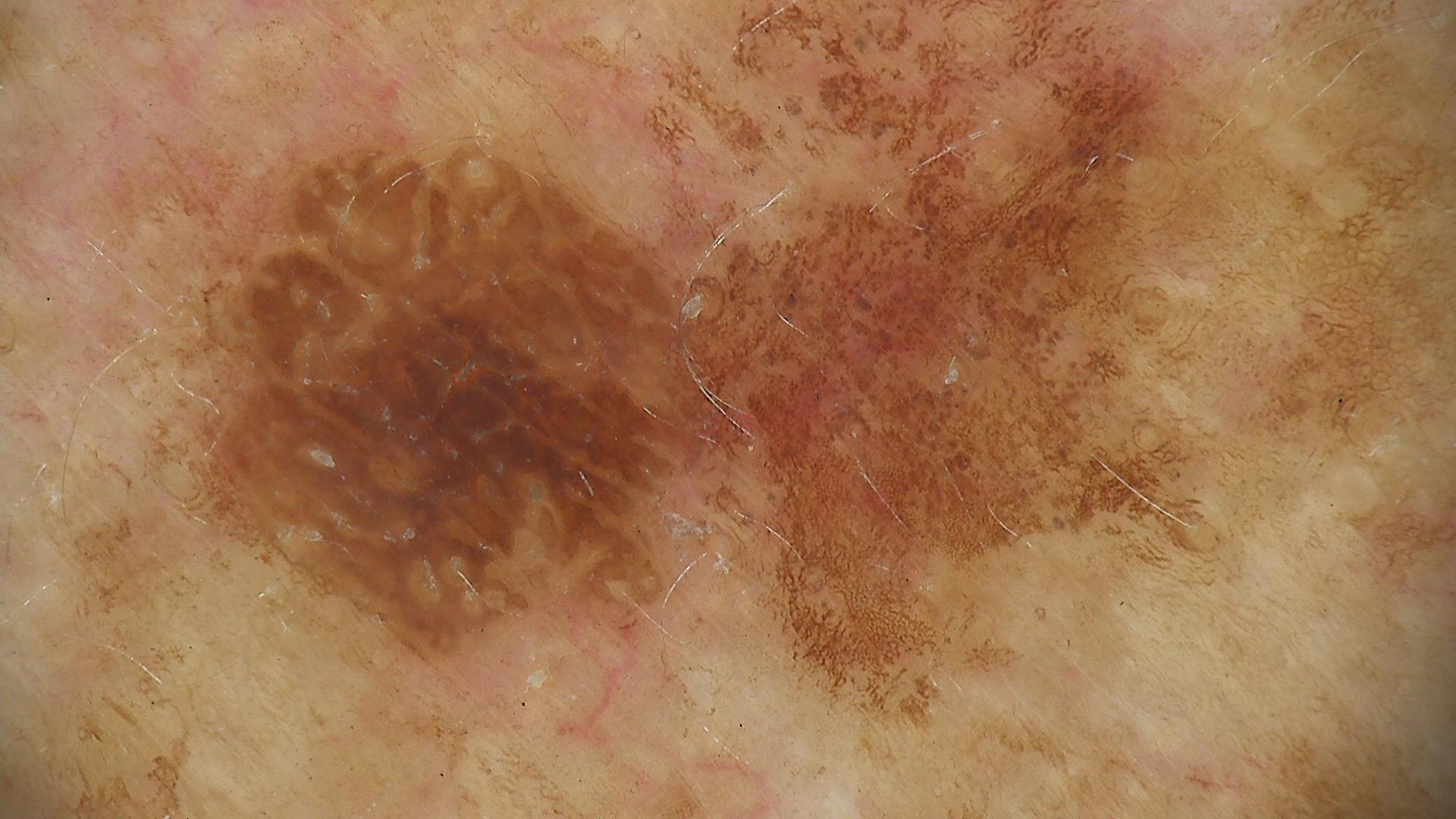Case:
A dermoscopic image of a skin lesion.
Impression:
The diagnosis was a keratinocytic lesion — a seborrheic keratosis.